The patient reports itching; the affected area is the leg; the patient reports the condition has been present for less than one week; the patient described the issue as a rash; this is a close-up image; texture is reported as raised or bumpy — 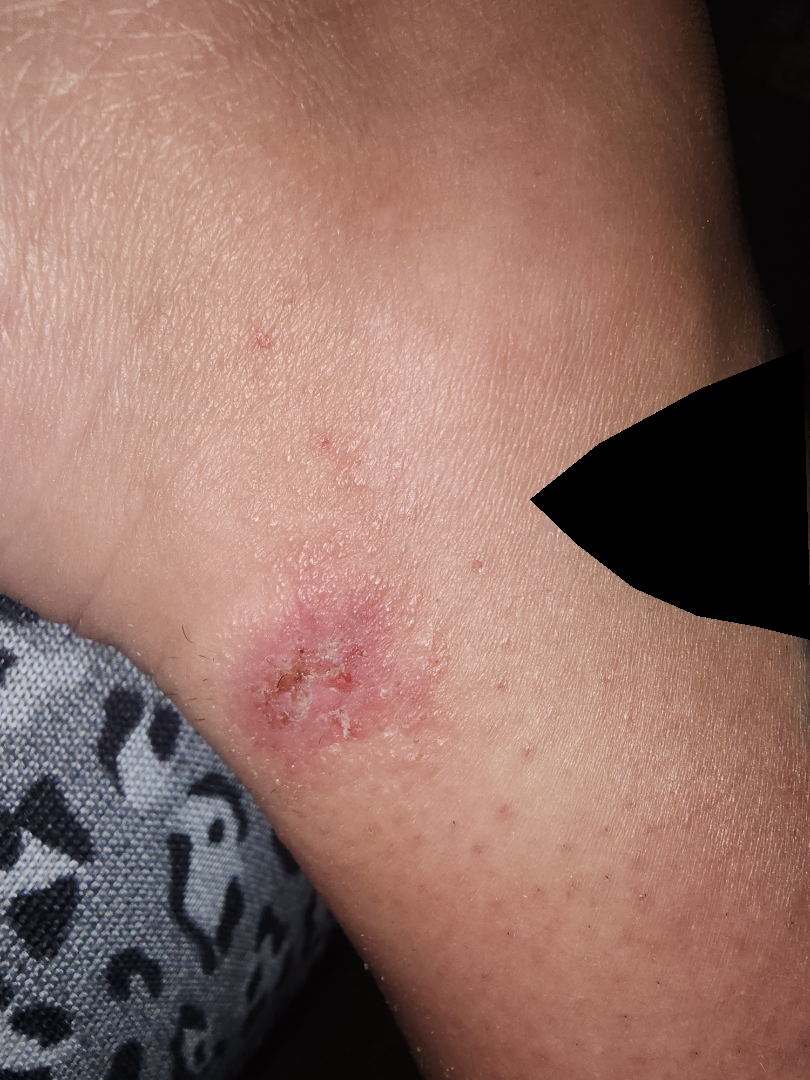The leading impression is Eczema.